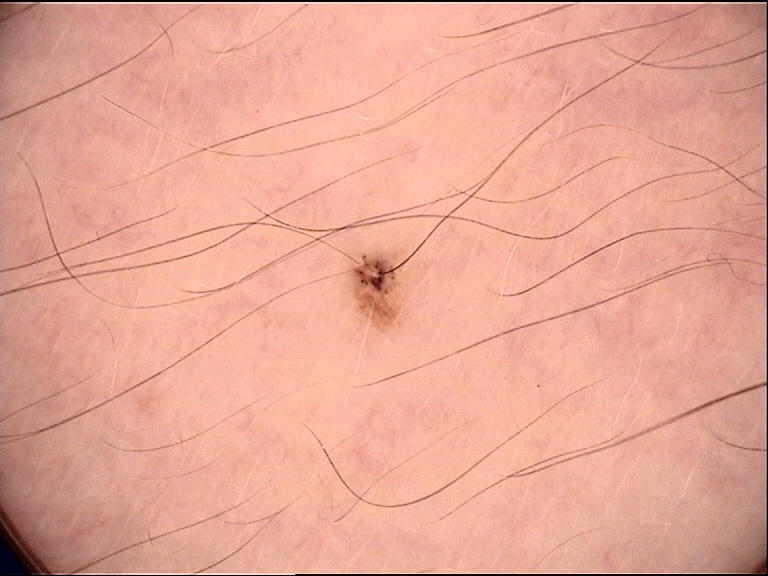Findings:
* image type: dermatoscopy
* class: dysplastic junctional nevus (expert consensus)